The chart notes tobacco use, pesticide exposure, prior skin cancer (patient or family), prior malignancy (patient or family), and alcohol use · a male patient 61 years old · a smartphone photograph of a skin lesion — 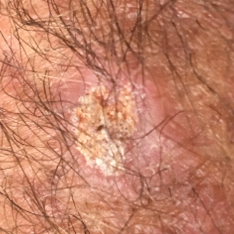The lesion is located on a forearm.
The lesion measures approximately 11 × 8 mm.
The patient reports that the lesion is elevated, itches, and hurts.
The biopsy diagnosis was a lesion of indeterminate malignant potential — an actinic keratosis.